The palm, back of the hand, head or neck and arm are involved; the patient described the issue as a rash; skin tone: Fitzpatrick phototype I; the lesion is associated with burning, bothersome appearance and darkening; female contributor, age 18–29; no relevant systemic symptoms; this image was taken at a distance; the condition has been present for less than one week; the lesion is described as raised or bumpy:
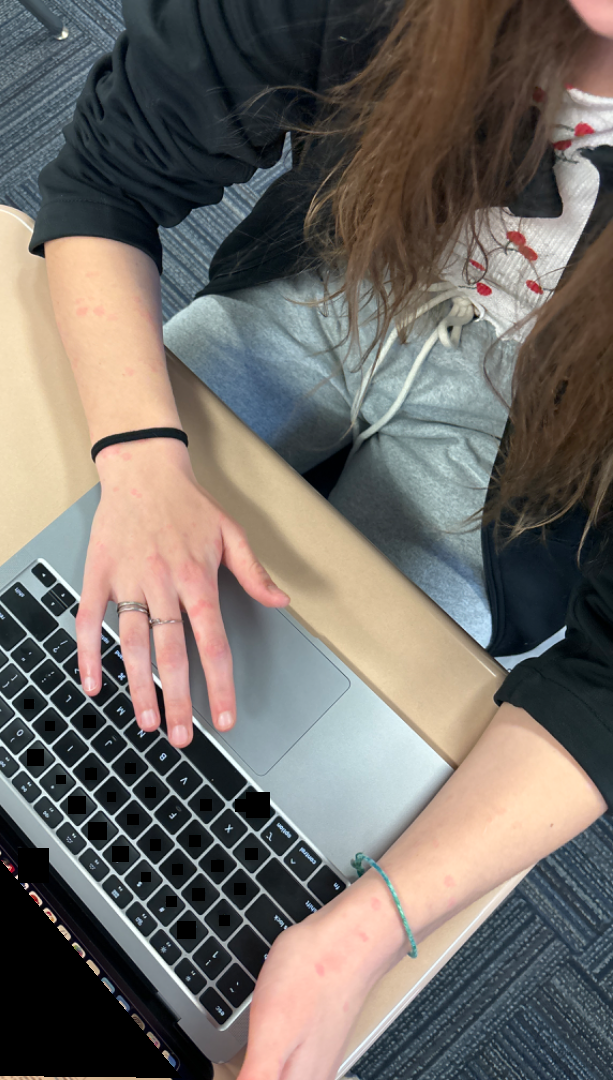Impression:
On dermatologist assessment of the image, Urticaria (most likely); Hypersensitivity (considered).